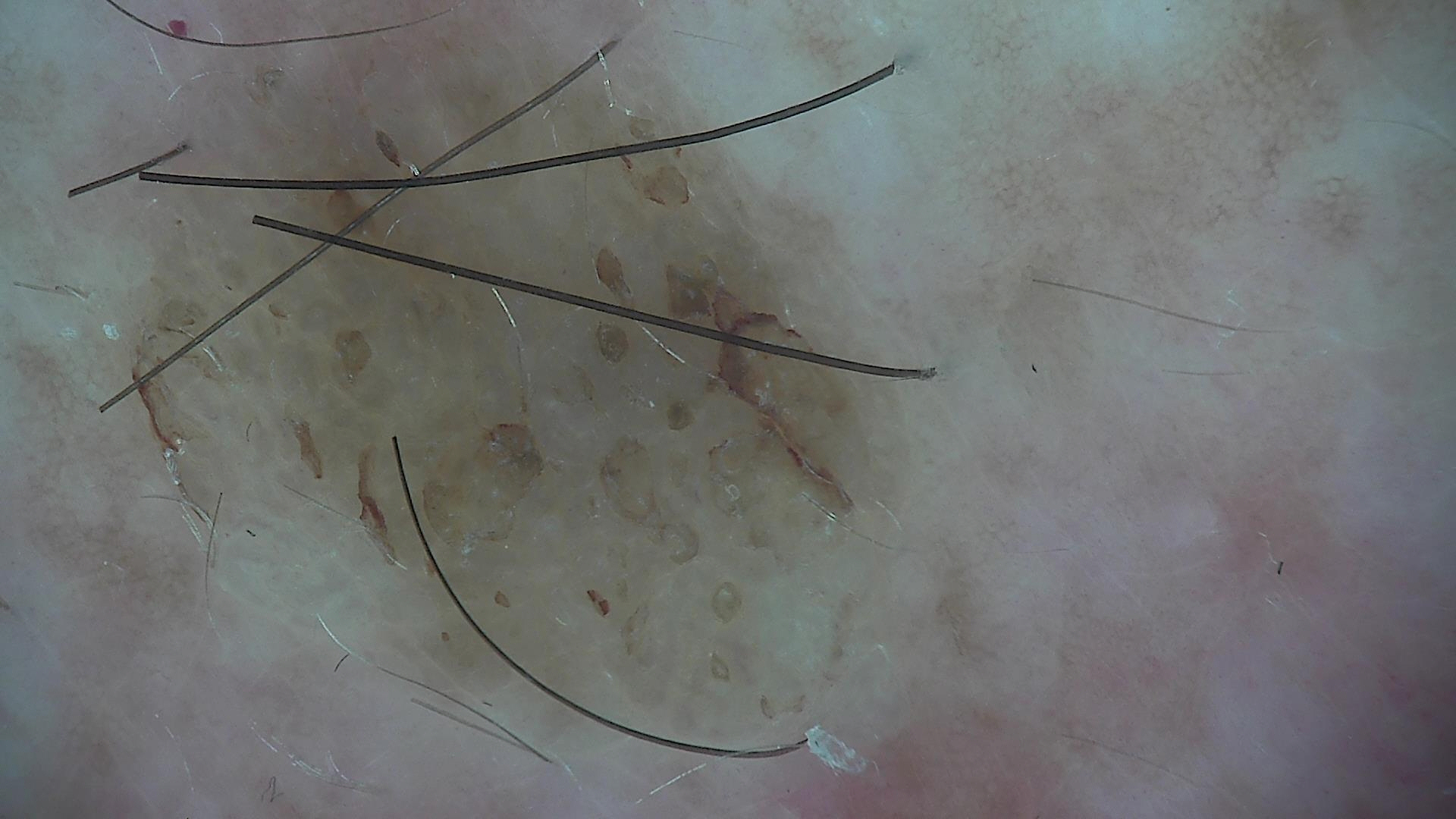Conclusion: Diagnosed as a keratinocytic lesion — a seborrheic keratosis.